The photograph is a close-up of the affected area; the patient reported no systemic symptoms; the patient notes the lesion is raised or bumpy; the affected area is the arm; the condition has been present for about one day; the lesion is associated with enlargement and itching; the patient considered this skin that appeared healthy to them:
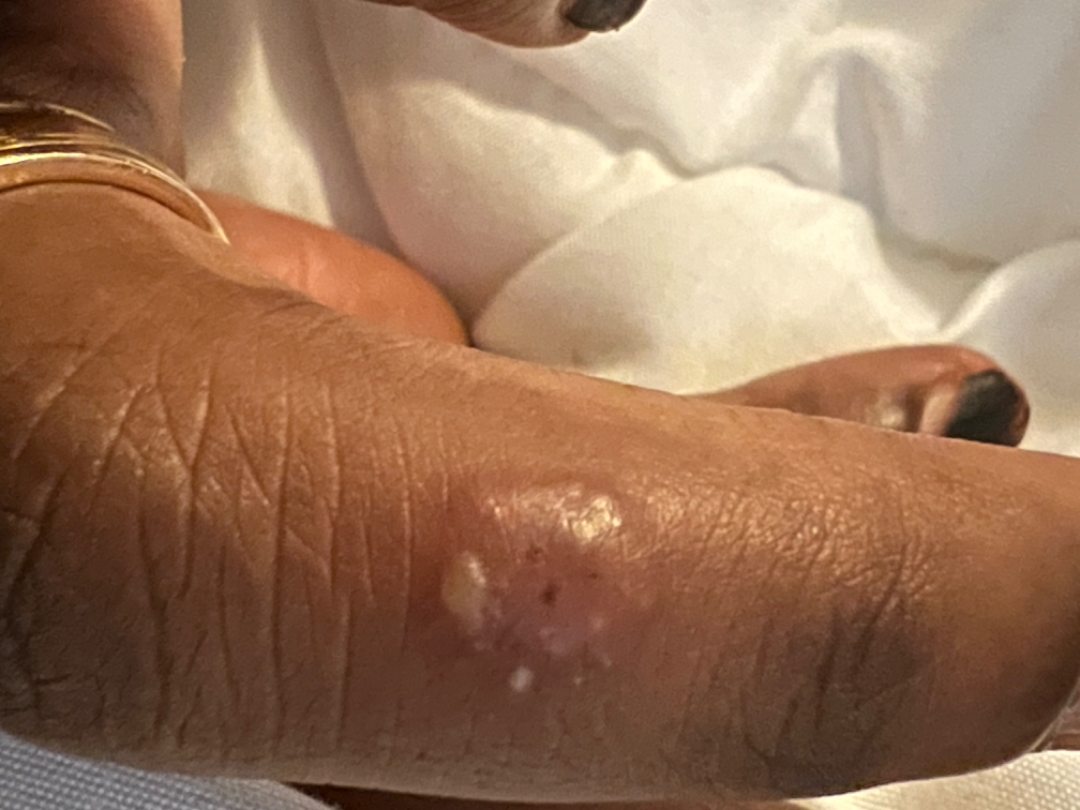Assessment:
The skin condition could not be confidently assessed from this image.